The contributor reports the lesion is raised or bumpy. The contributor reports the condition has been present for about one day. This image was taken at a distance. Located on the head or neck and arm. Symptoms reported: itching — 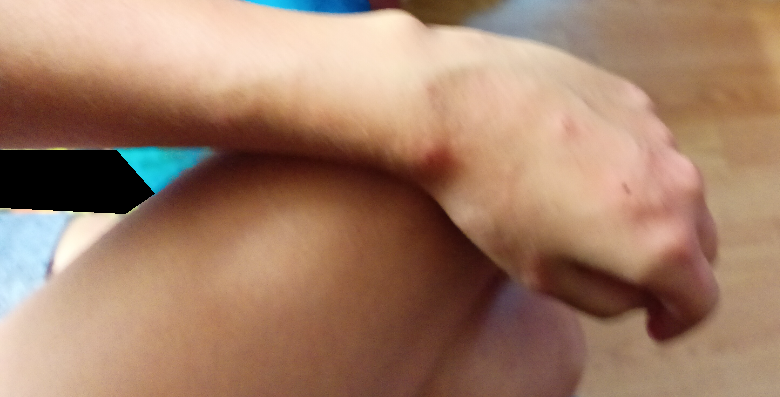Findings:
The dermatologist could not determine a likely condition from the photograph alone.